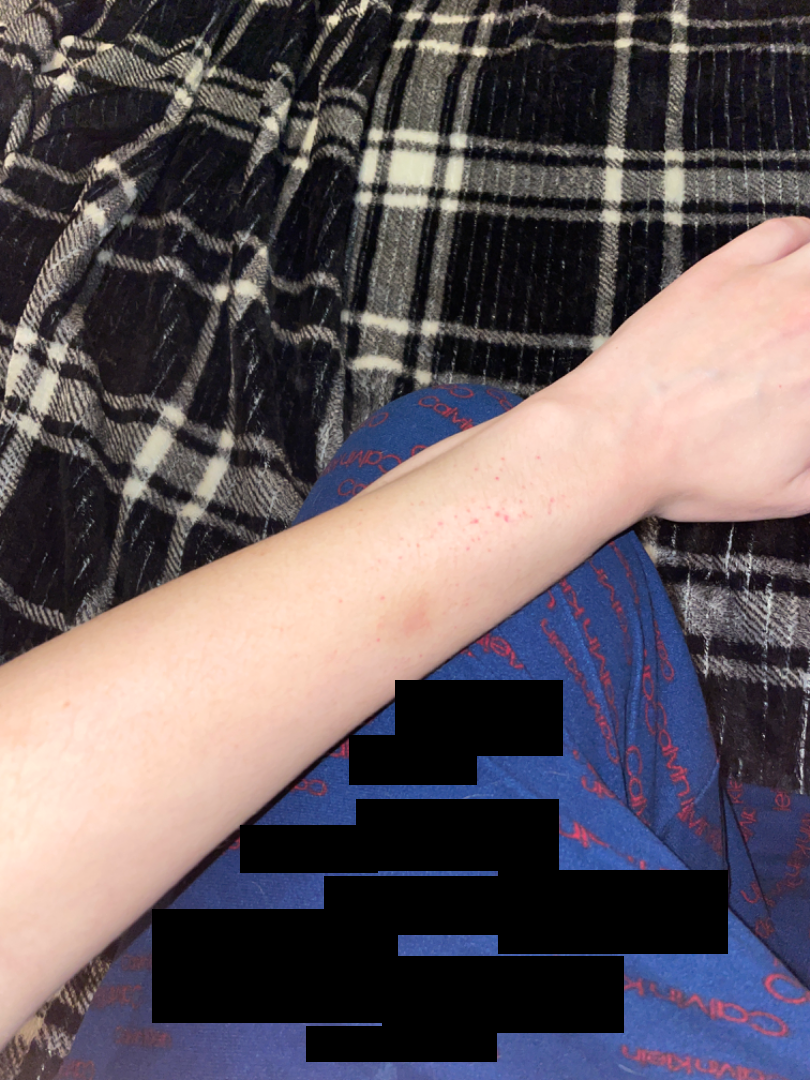{
  "differential": {
    "leading": [
      "petechiae"
    ],
    "considered": [
      "Pigmented purpuric eruption",
      "Leukocytoclastic Vasculitis"
    ]
  }
}